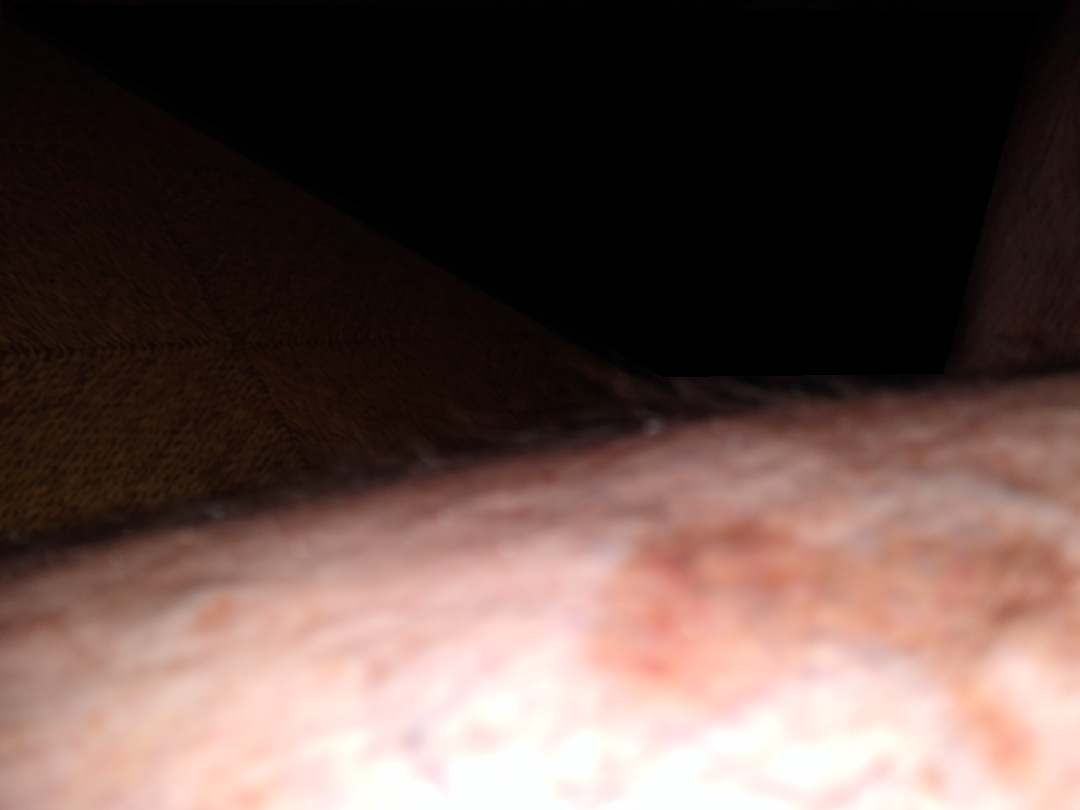Texture is reported as flat.
The lesion is associated with bothersome appearance.
The affected area is the leg.
The patient described the issue as a growth or mole.
Reported duration is more than one year.
The contributor reports associated fatigue.
The photo was captured at an angle.
Male contributor, age 60–69.
On remote review of the image, consistent with Pigmented purpuric eruption.